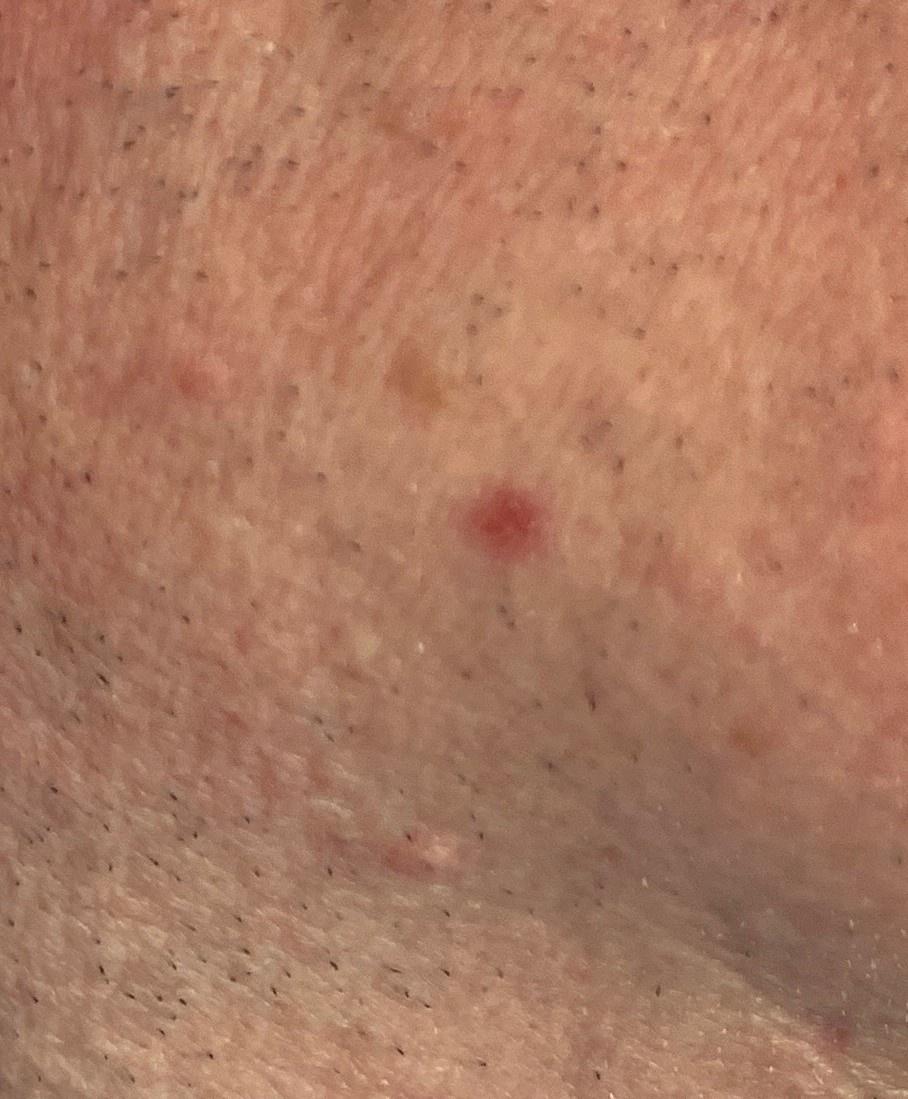A wide-field clinical photograph of a skin lesion. The lesion is located on the head or neck. Confirmed on histopathology as a basal cell carcinoma.